A female subject, aged around 55 · a dermoscopic close-up of a skin lesion:
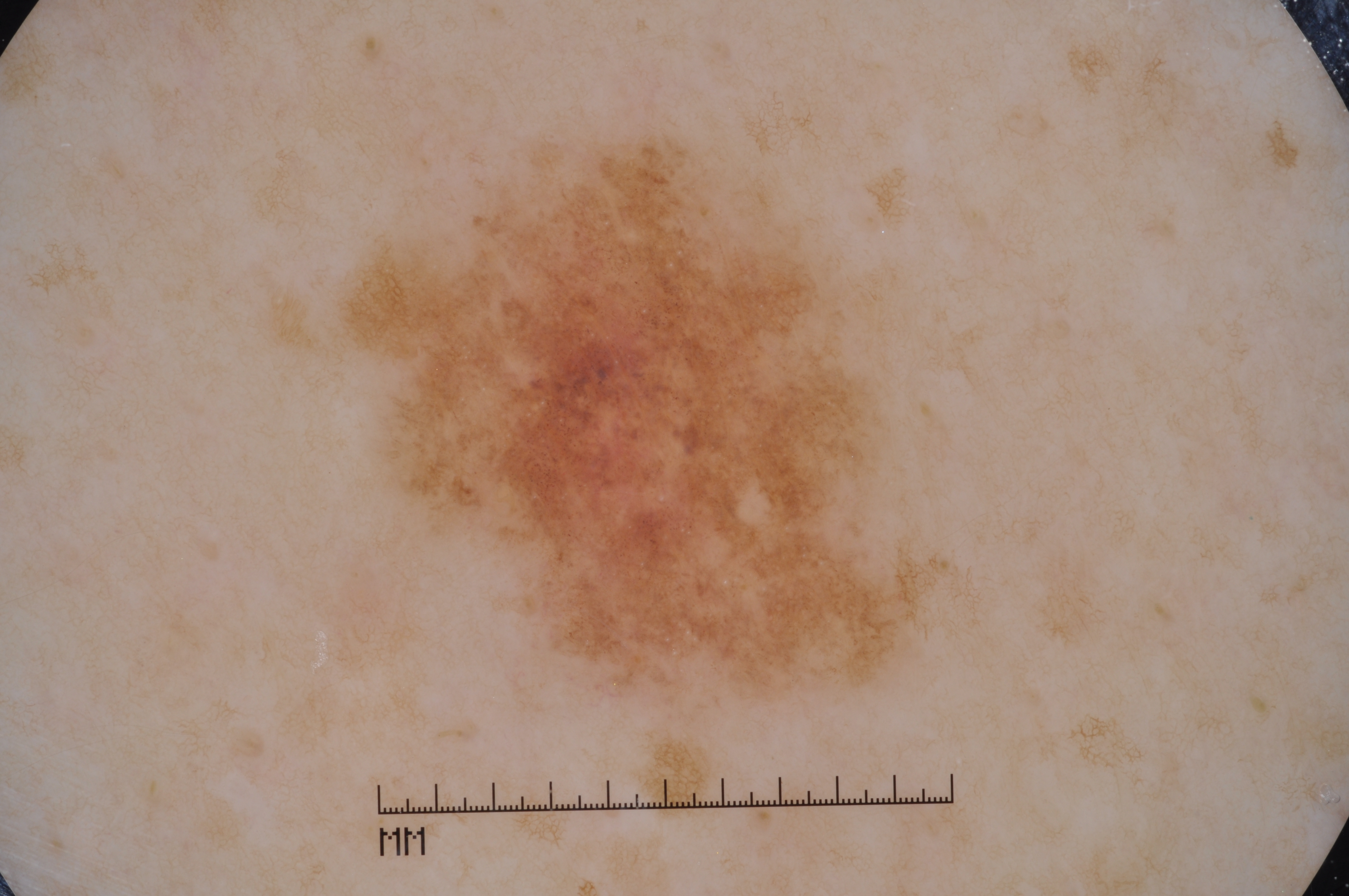lesion location: 348, 133, 938, 693; dermoscopic features: milia-like cysts and pigment network; lesion extent: moderate; diagnostic label: a melanocytic nevus, a benign lesion.